The affected area is the front of the torso and back of the torso; the photo was captured at a distance; reported duration is more than one year; the patient considered this a rash:
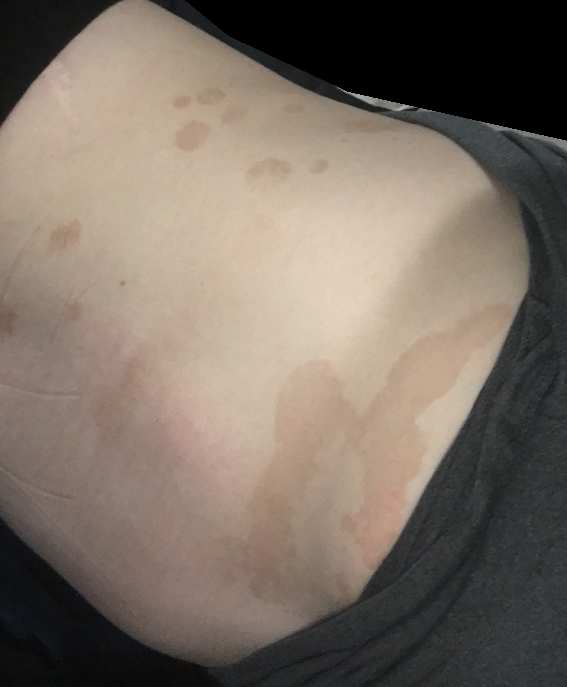| feature | finding |
|---|---|
| assessment | indeterminate from the photograph |